A dermoscopic close-up of a skin lesion.
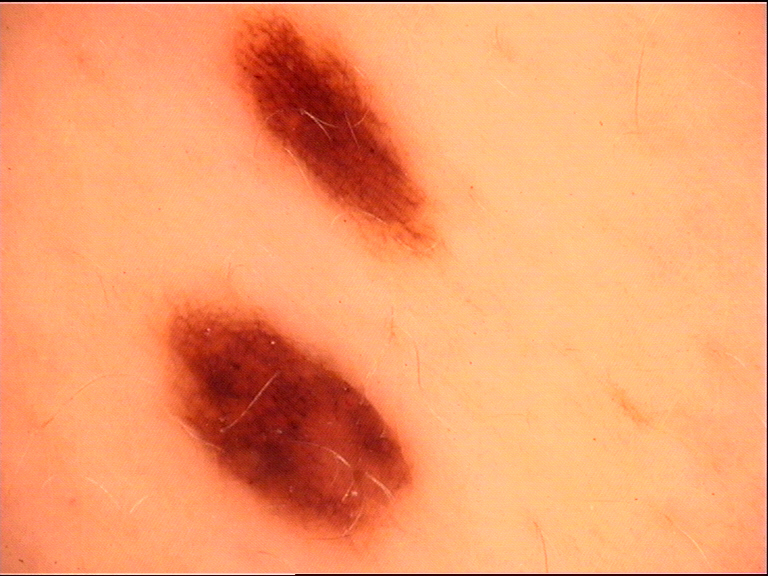Findings:
* diagnosis: dysplastic junctional nevus (expert consensus)